A dermoscopic image of a skin lesion.
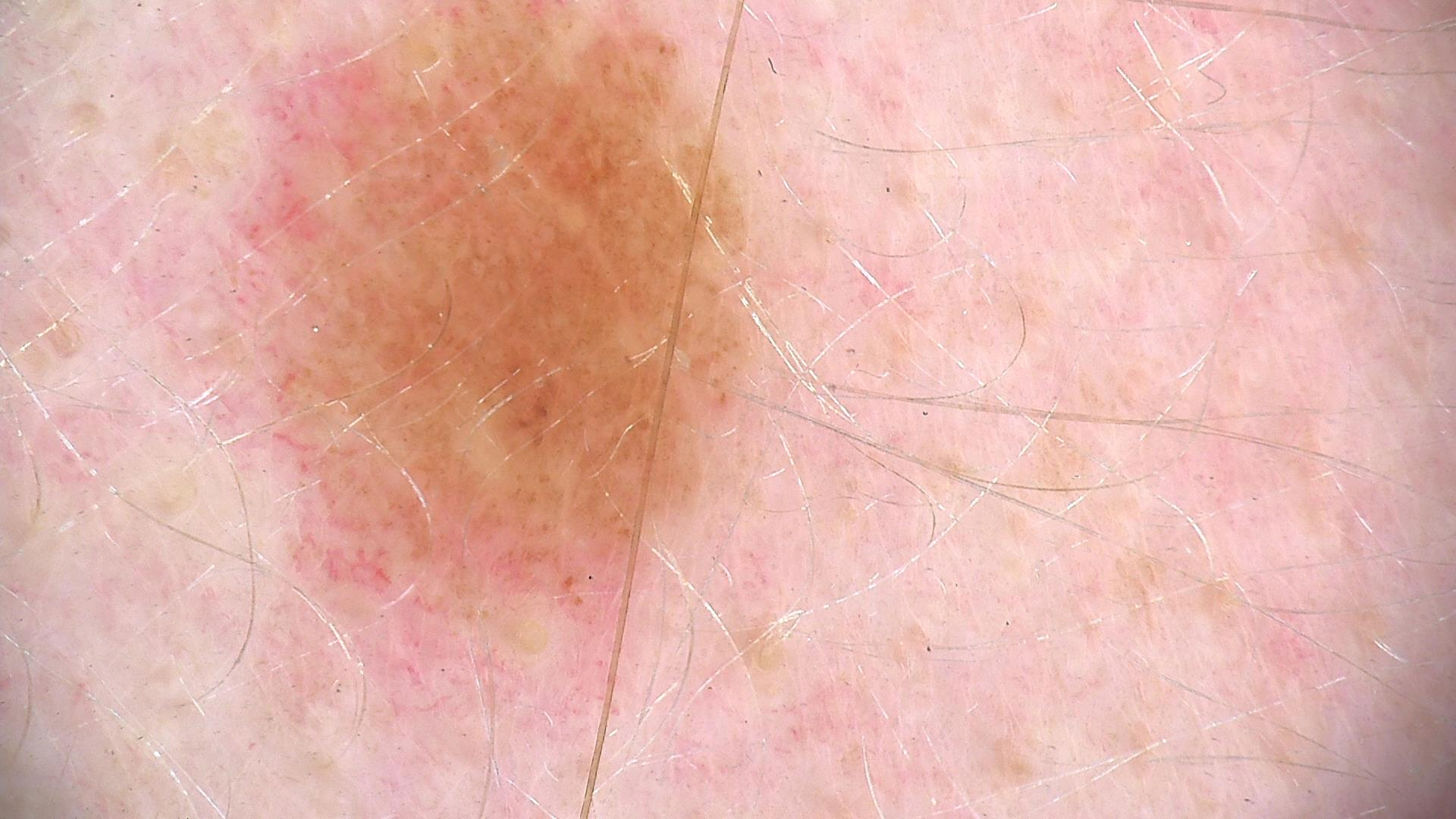label=dysplastic junctional nevus (expert consensus).